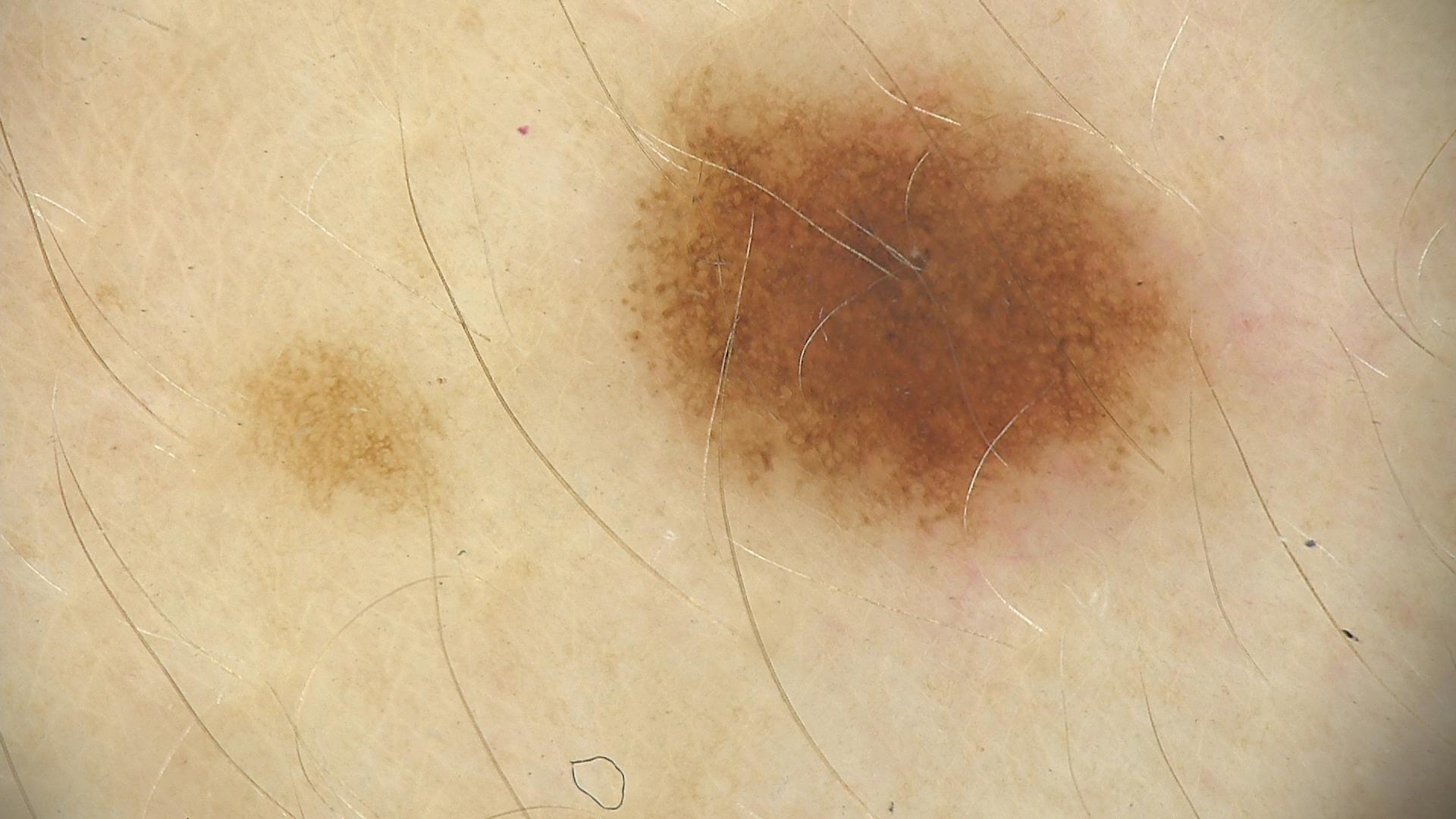A dermoscopic close-up of a skin lesion. Labeled as a benign lesion — a dysplastic junctional nevus.